The photograph was taken at an angle:
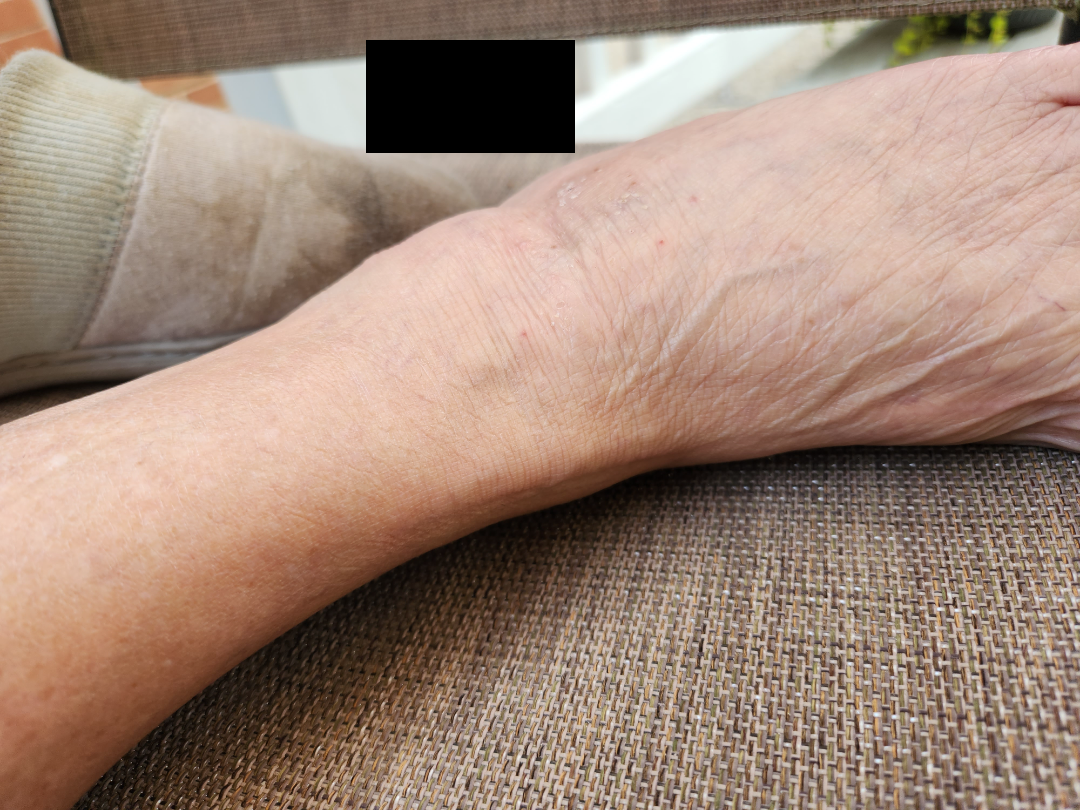{"differential": "Lichen Simplex Chronicus"}